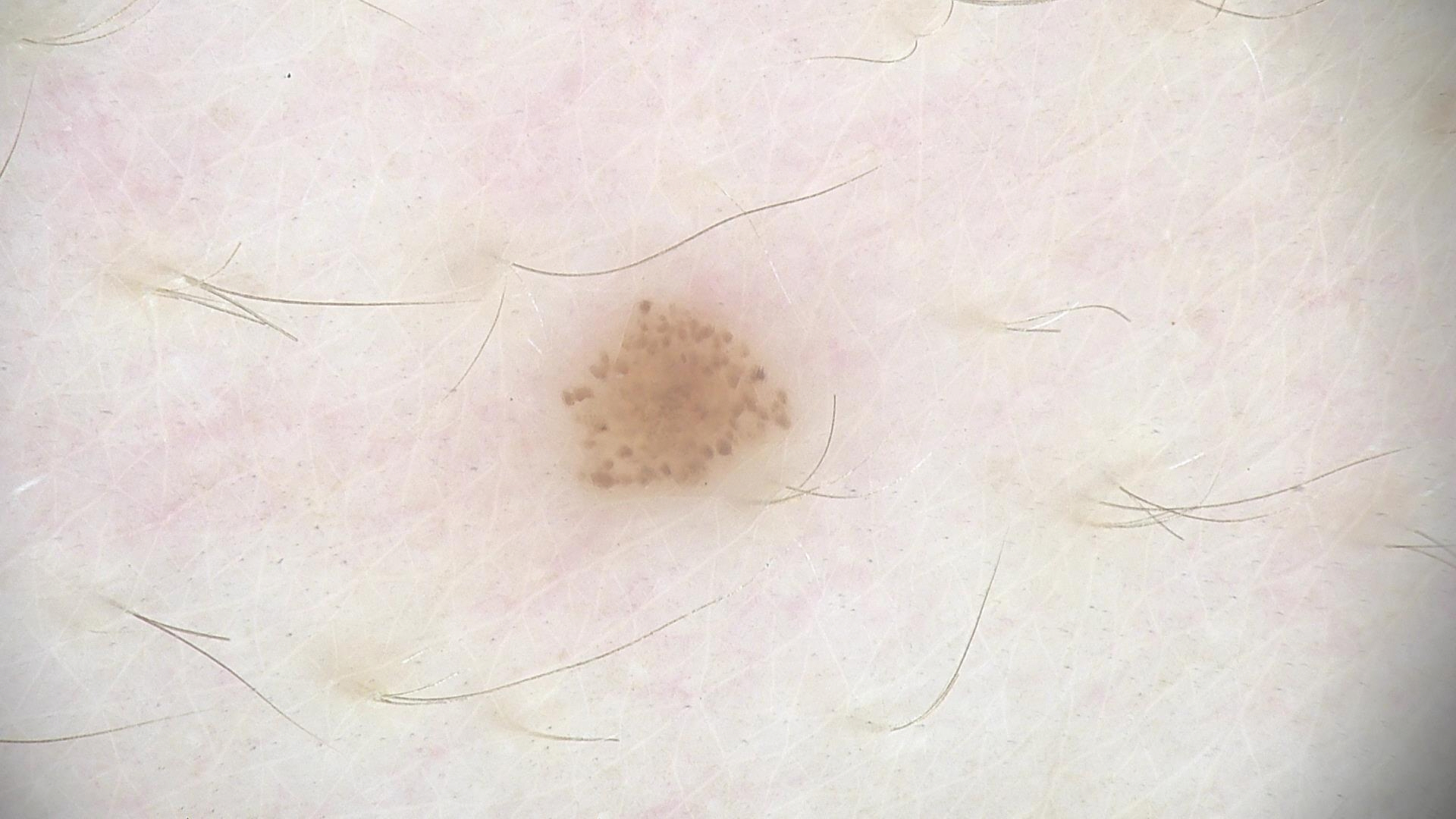The diagnosis was a benign lesion — a dysplastic junctional nevus.